The photograph was taken at a distance. Female patient, age 18–29. The affected area is the leg and front of the torso: 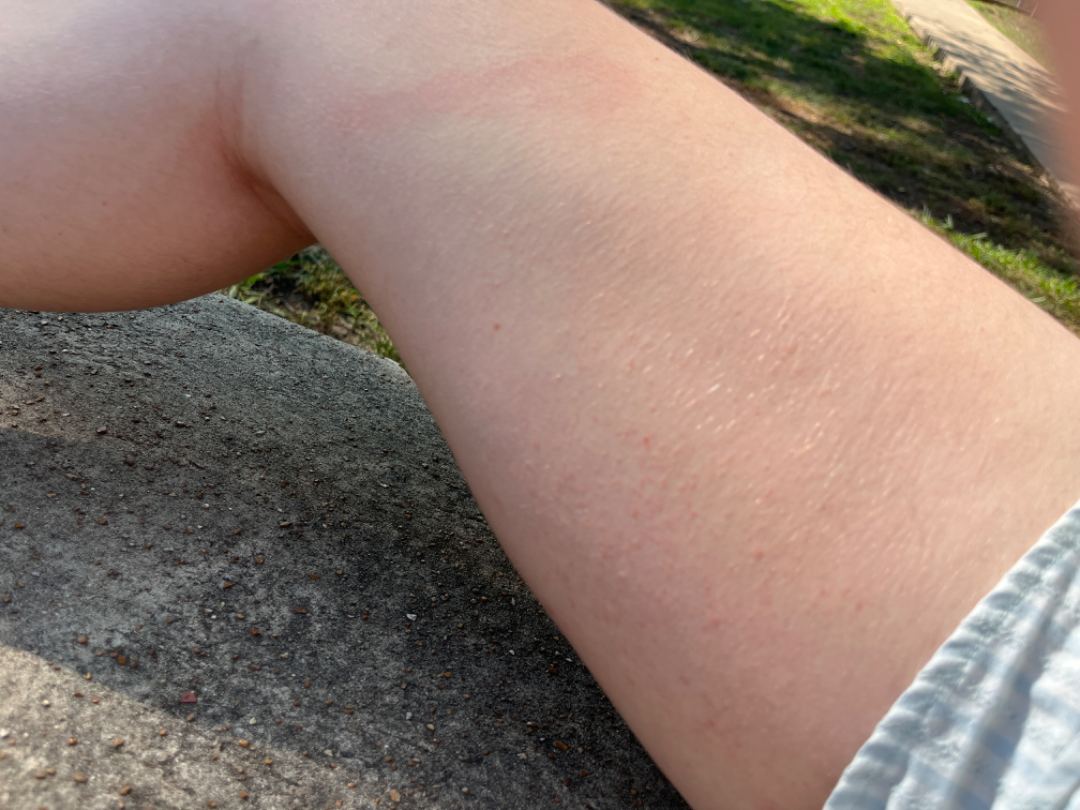dermatologist impression: most consistent with Keratosis pilaris.